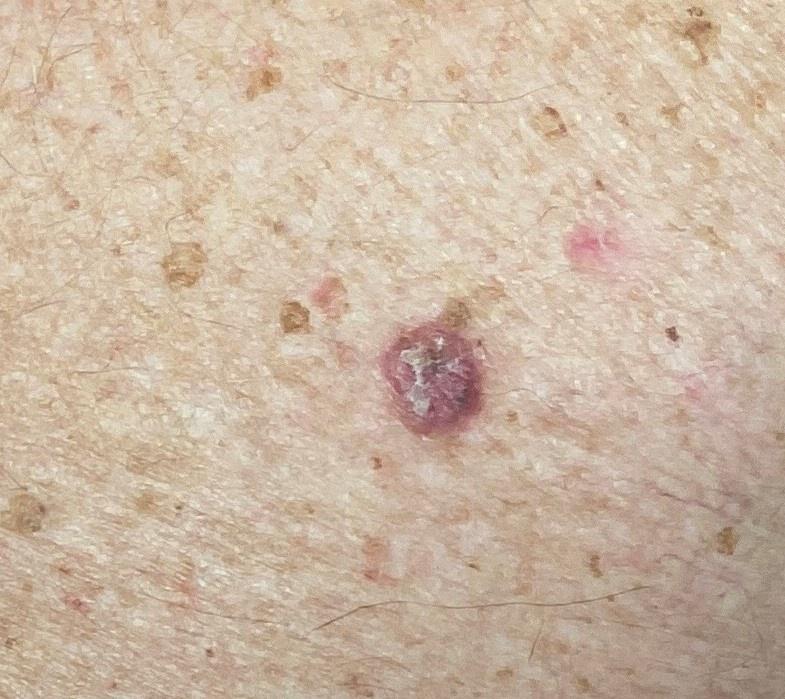{"image": "clinical photograph", "skin_type": "II", "patient": {"age_approx": 80, "sex": "male"}, "lesion_location": {"region": "the trunk", "detail": "the posterior trunk"}, "diagnosis": {"name": "Basal cell carcinoma", "malignancy": "malignant", "confirmation": "histopathology", "lineage": "adnexal"}}